The patient is Fitzpatrick skin type II. A male subject in their mid- to late 60s.
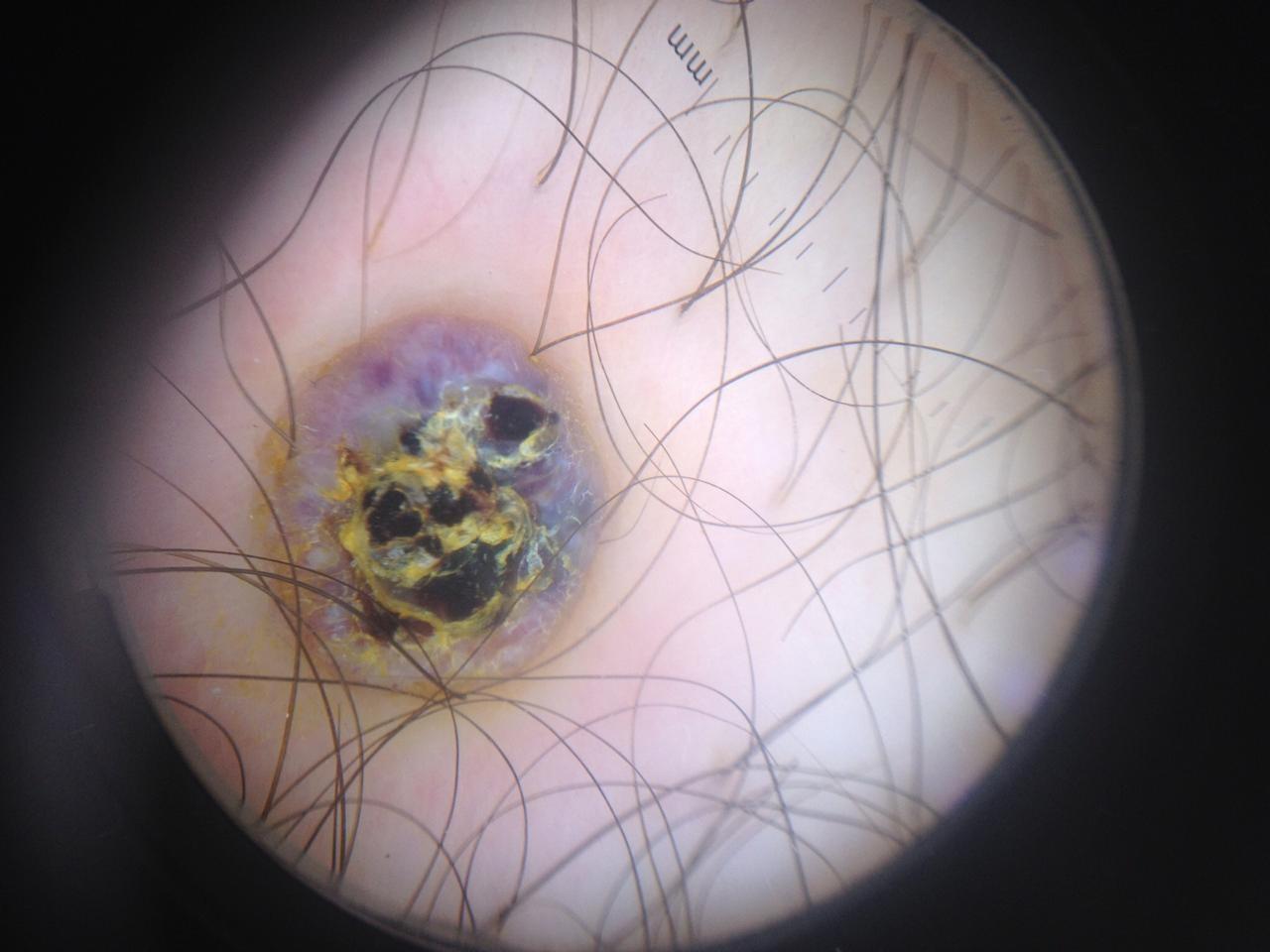On biopsy, the diagnosis was a vascular lesion.